A dermatoscopic image of a skin lesion.
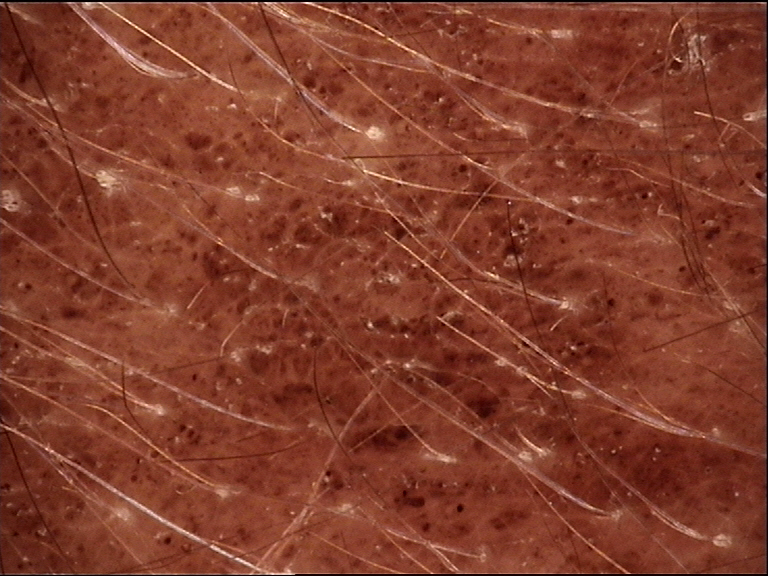Labeled as a banal lesion — a congenital compound nevus.